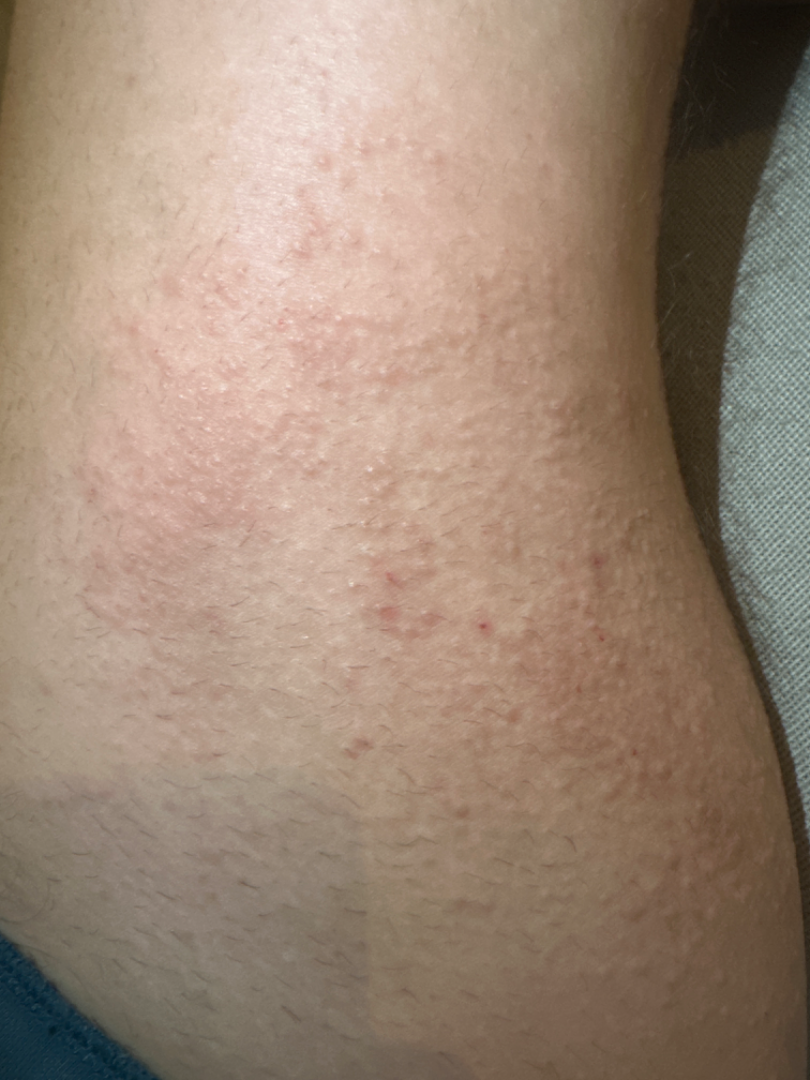{
  "shot_type": "close-up",
  "body_site": "leg",
  "symptoms": [
    "burning",
    "enlargement",
    "itching"
  ],
  "skin_tone": {
    "fitzpatrick": "IV"
  },
  "texture": "raised or bumpy",
  "duration": "one to four weeks",
  "patient": "male",
  "patient_category": "a rash",
  "differential": {
    "tied_lead": [
      "Cutaneous T Cell Lymphoma",
      "Eczema"
    ]
  }
}